A dermoscopic close-up of a skin lesion; a male subject in their mid- to late 60s:
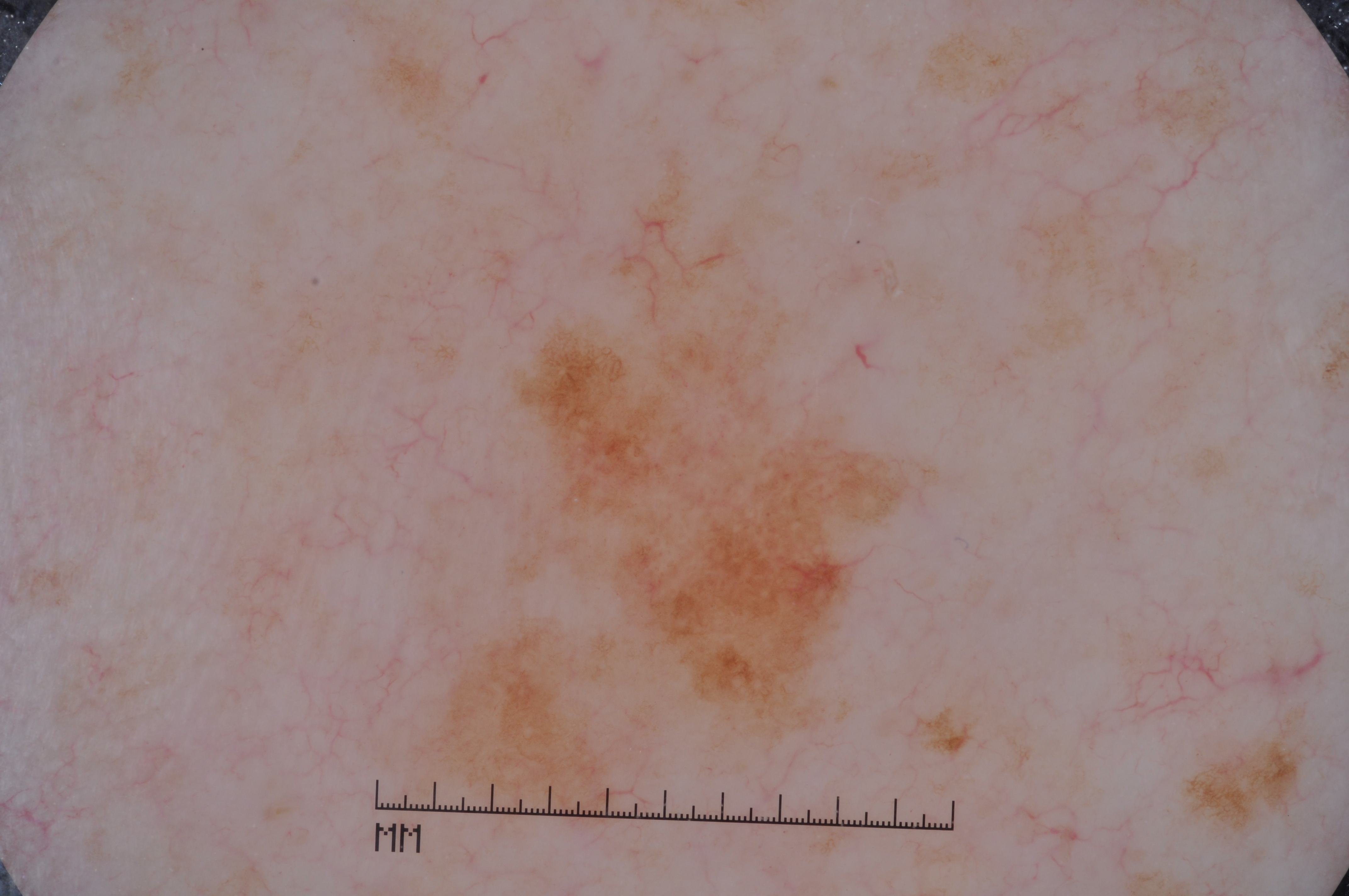Findings:
* dermoscopic features: milia-like cysts, negative network, and pigment network
* lesion bbox: bbox(383, 161, 966, 857)
* diagnosis: a melanocytic nevus